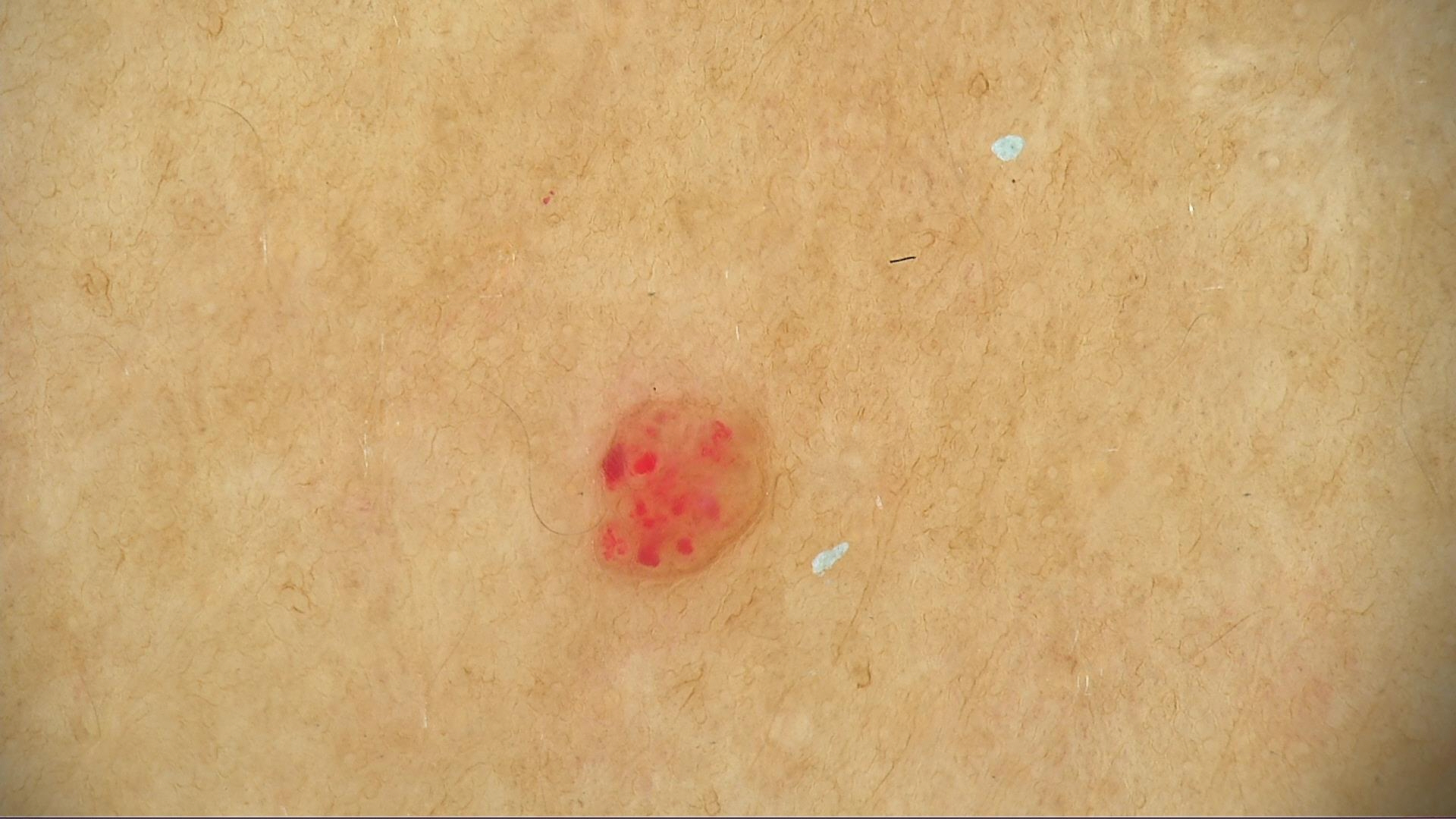diagnostic label: hemangioma (expert consensus)